Dermoscopy of a skin lesion:
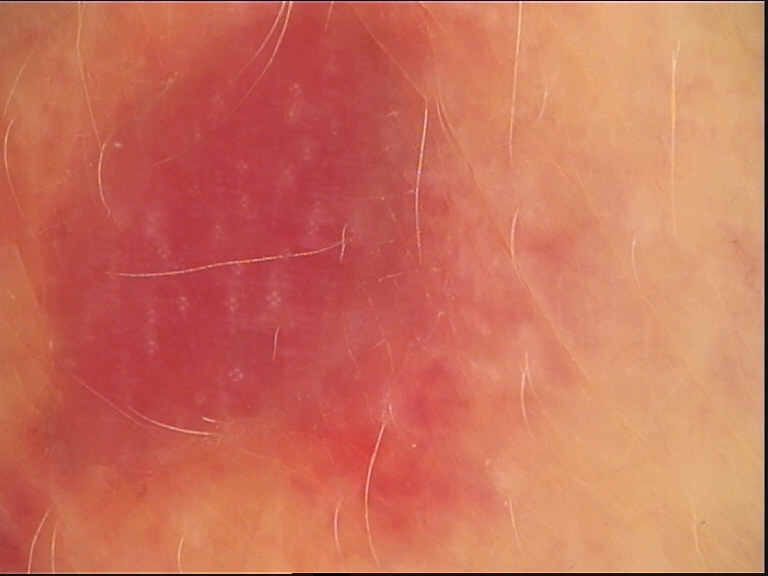Diagnosed as a keratinocytic lesion — an actinic keratosis.